A clinical close-up photograph of a skin lesion. A patient age 60: 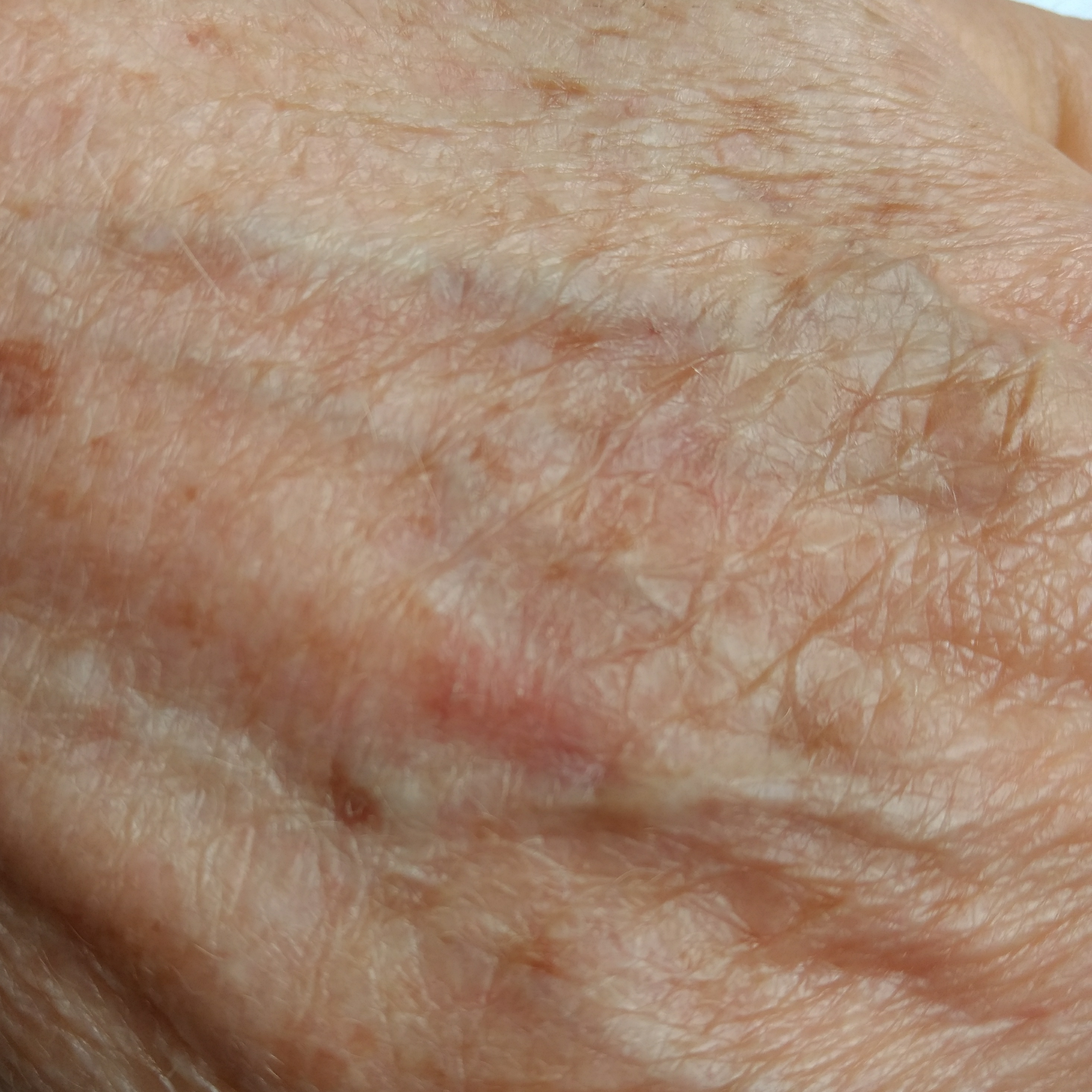Case summary: The lesion involves a hand. The patient reports that the lesion has not grown. Impression: Diagnosed by dermatologist consensus as an actinic keratosis.